A smartphone photograph of a skin lesion · by history, alcohol use and pesticide exposure · a male patient 47 years old.
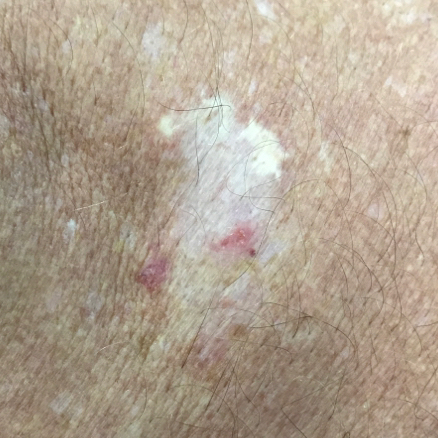Case summary: The lesion is on the back. Measuring about 16 × 10 mm. Per patient report, the lesion has bled, itches, has grown, and is elevated. Conclusion: Histopathological examination showed a skin cancer — a basal cell carcinoma.